The lesion is described as rough or flaky and raised or bumpy. The patient reported no systemic symptoms. The patient considered this a rash. An image taken at an angle. The arm is involved.
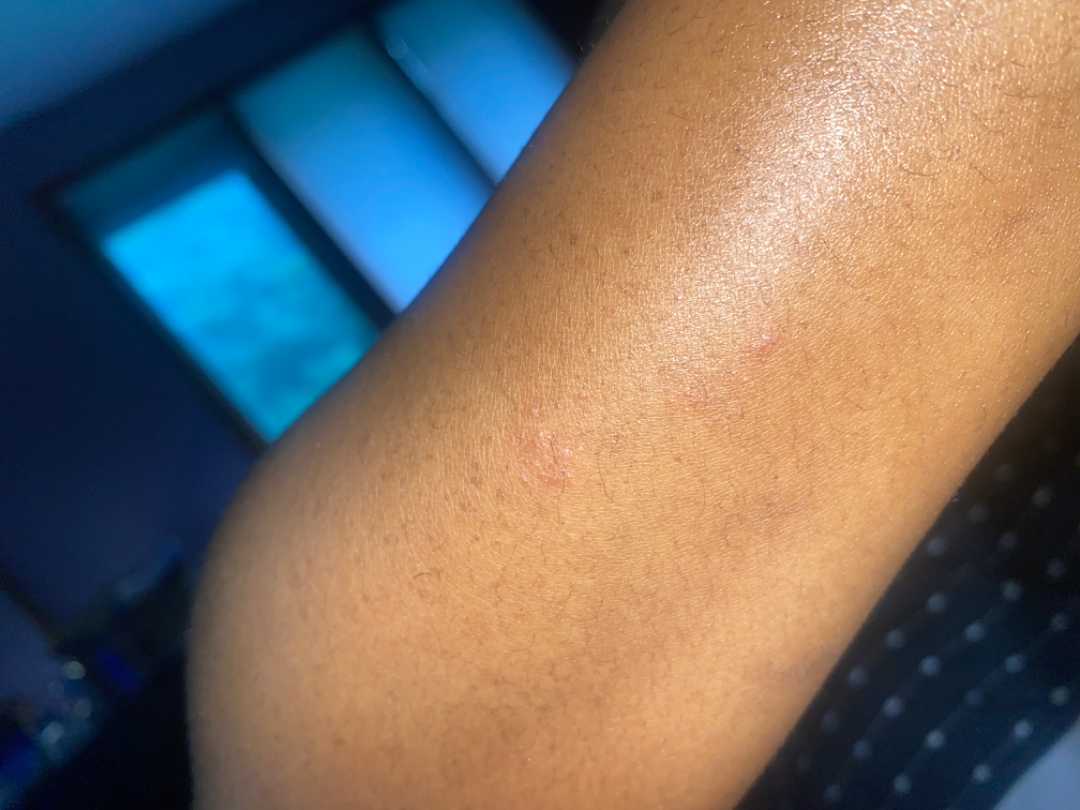assessment: could not be assessed